The lesion involves the front of the torso, arm, top or side of the foot and leg · the contributor is 18–29, female · an image taken at an angle:
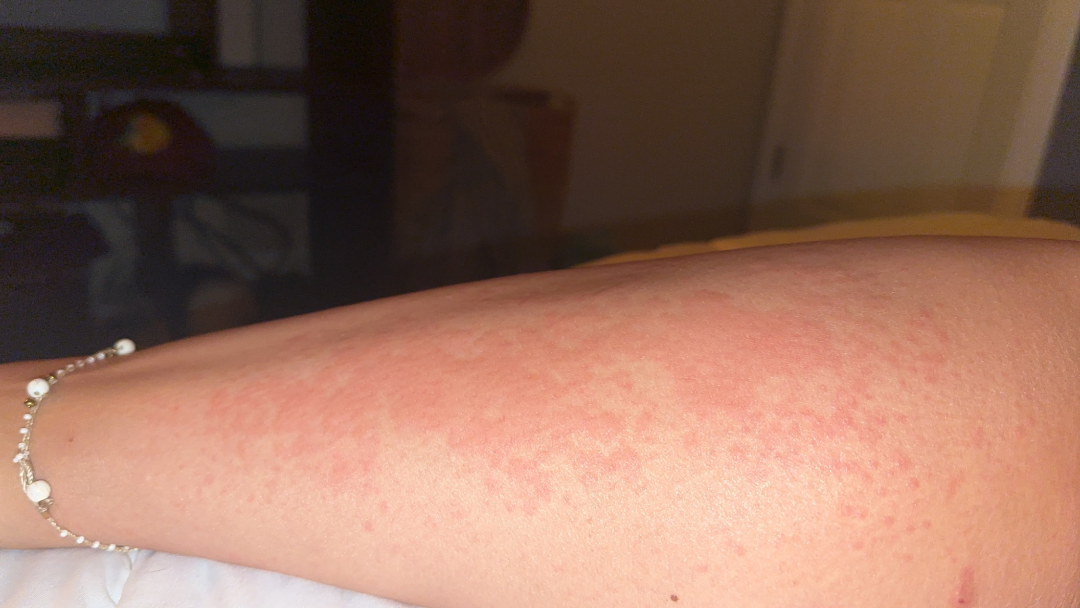Patient information:
The contributor reports associated shortness of breath and fatigue. FST IV; human graders estimated Monk skin tone scale 5 (US pool) or 3 (India pool). The contributor reports the lesion is raised or bumpy. The contributor reports itching.
Review:
Most likely Allergic Contact Dermatitis; also consider Urticaria; a remote consideration is Eczema.